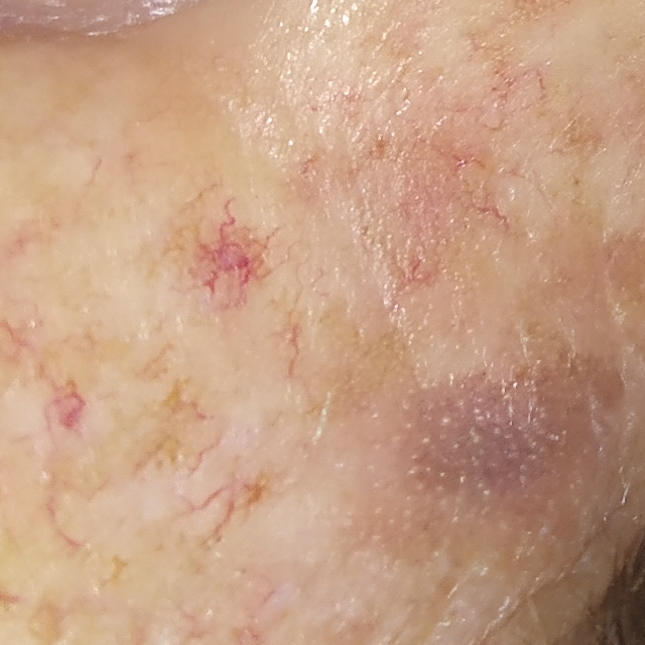Patient and lesion:
A female subject aged 67. A clinical photograph showing a skin lesion. FST III. The chart notes pesticide exposure, tobacco use, and no alcohol use. The lesion is on the nose. The lesion measures approximately 3 × 3 mm. By the patient's account, the lesion does not itch.
Pathology:
The biopsy diagnosis was a malignant skin lesion — a basal cell carcinoma.